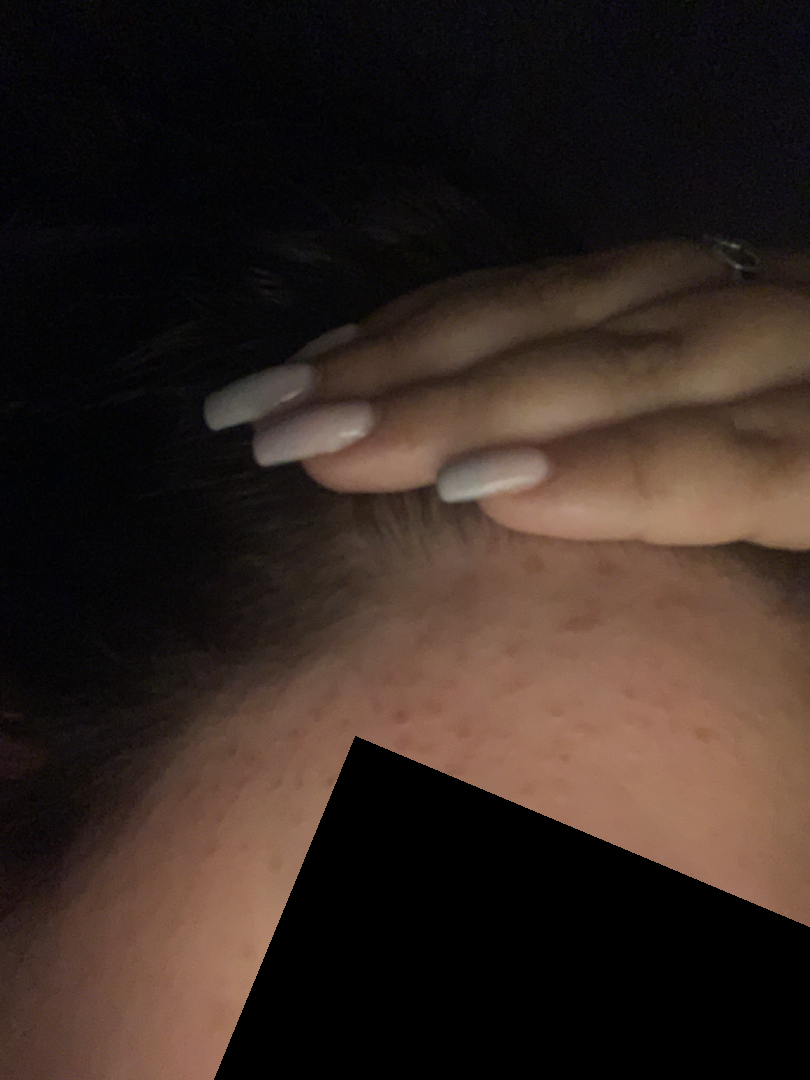The skin findings could not be characterized from the image.